The patient is FST III · the chart notes prior skin cancer (patient or family), prior malignancy (patient or family), and pesticide exposure · a smartphone photograph of a skin lesion · a male subject 52 years of age.
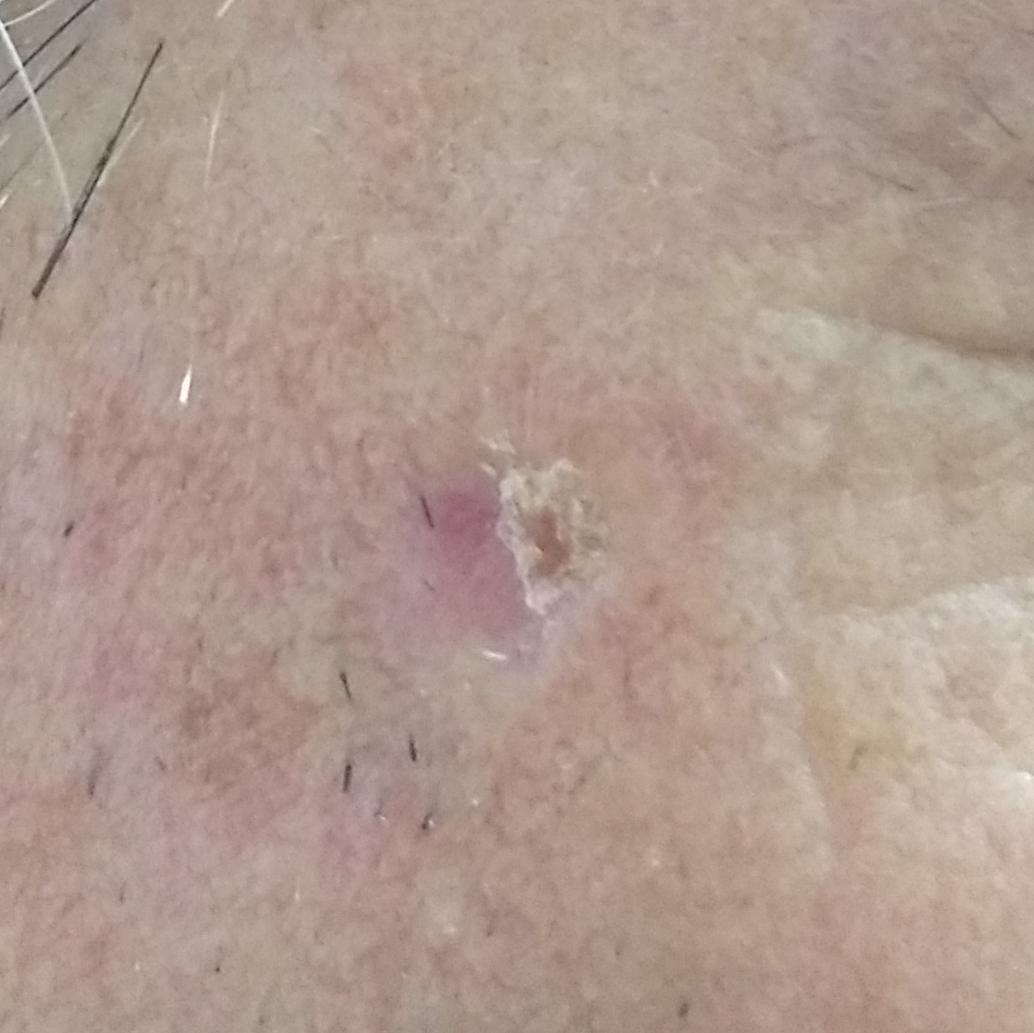| field | value |
|---|---|
| anatomic site | the face |
| diameter | approx. 3 × 3 mm |
| patient-reported symptoms | growth, elevation, itching, pain |
| diagnosis | basal cell carcinoma (biopsy-proven) |